A dermoscopic image of a skin lesion: 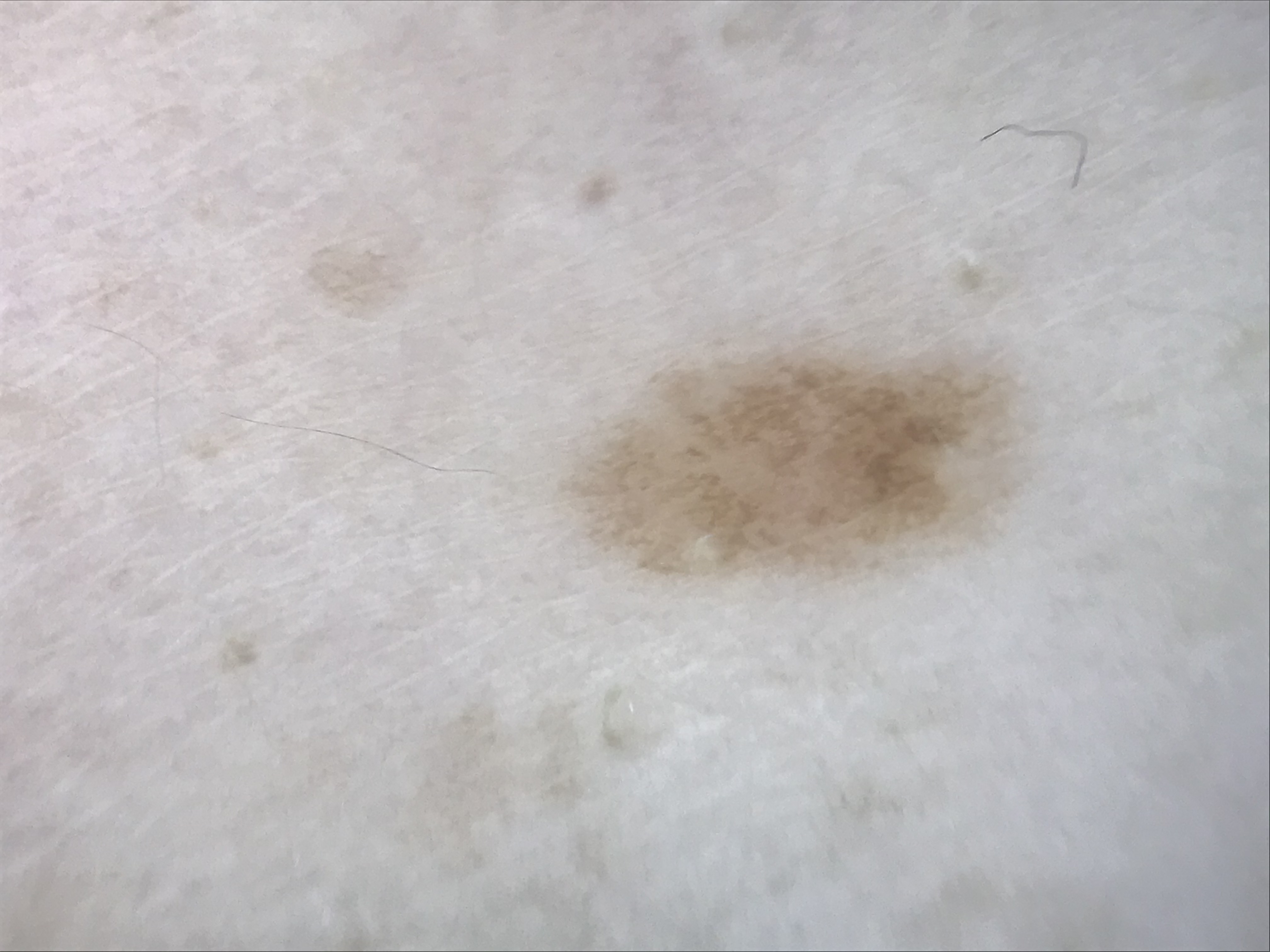* label: junctional nevus (expert consensus)